Close-up view. No associated lesion symptoms were reported. Located on the arm. The contributor notes the lesion is flat. Female contributor, age 18–29. The contributor notes the condition has been present for about one day.
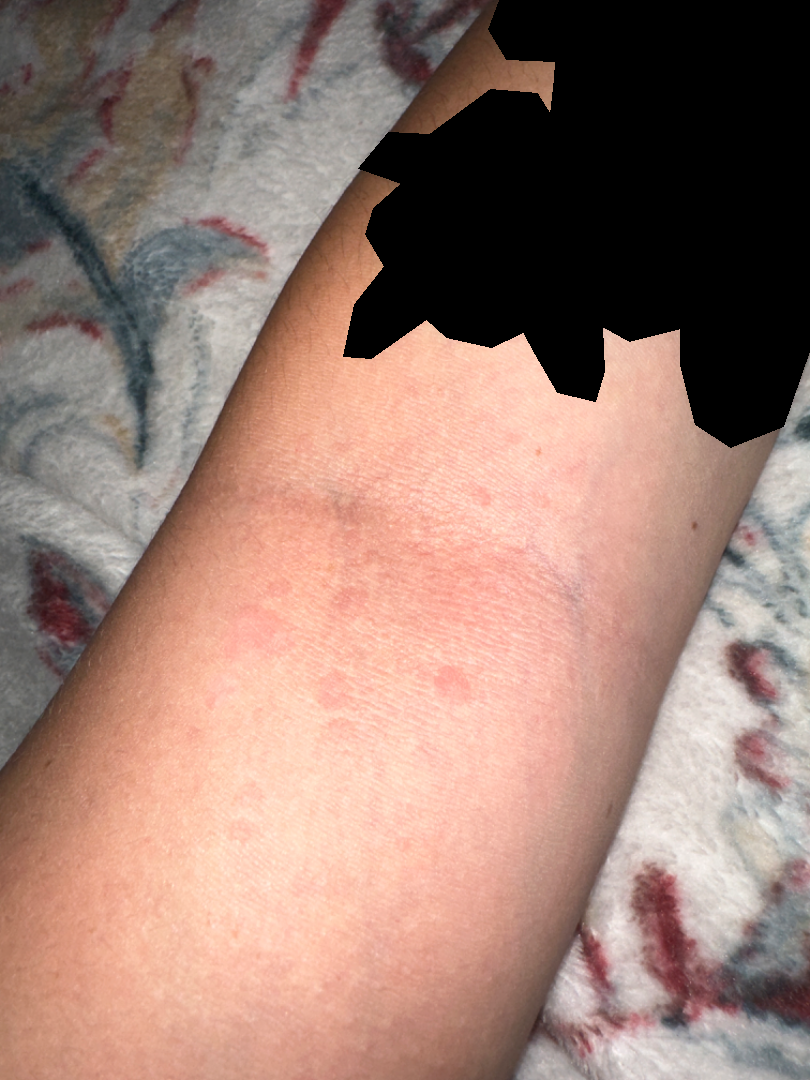Findings:
On remote review of the image, Tinea Versicolor (primary); Urticaria (possible); Eczema (unlikely); Insect Bite (unlikely); Psoriasis (unlikely).